A dermoscopic close-up of a skin lesion; a female patient, approximately 55 years of age.
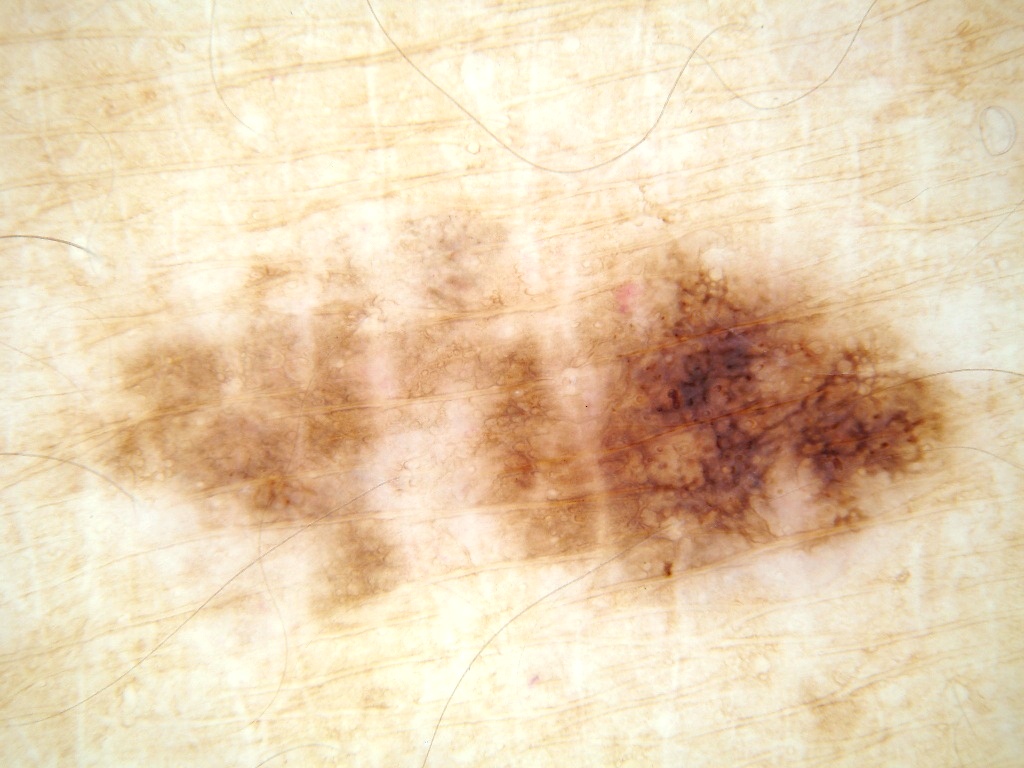Dermoscopy demonstrates pigment network and milia-like cysts.
The lesion is bounded by x1=24 y1=180 x2=996 y2=641.
Histopathology confirmed a melanoma, a malignancy.